A clinical photograph showing a skin lesion; a male subject 67 years of age: 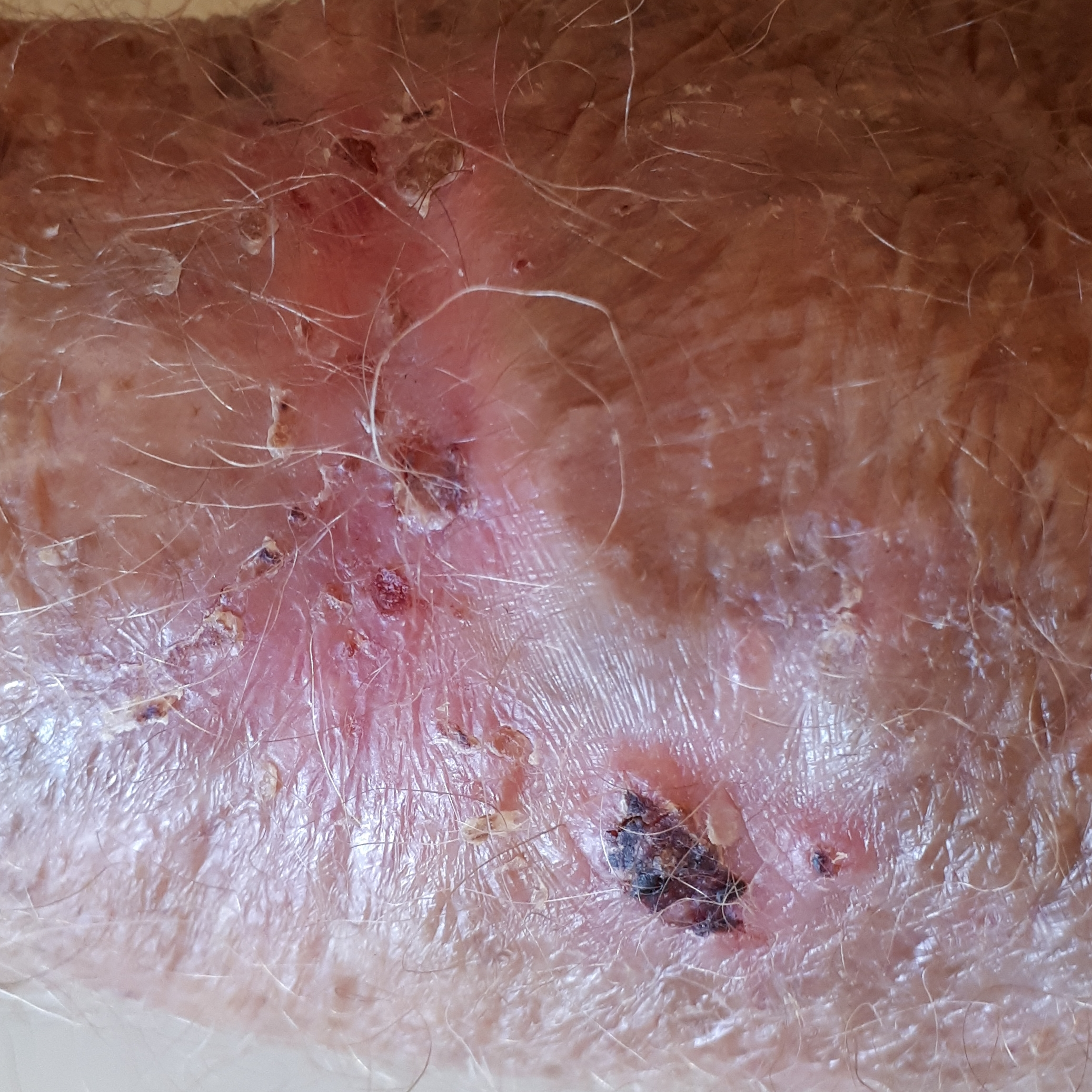Located on a forearm. The patient reports that the lesion has bled, itches, has changed, and has grown. Histopathological examination showed a basal cell carcinoma.